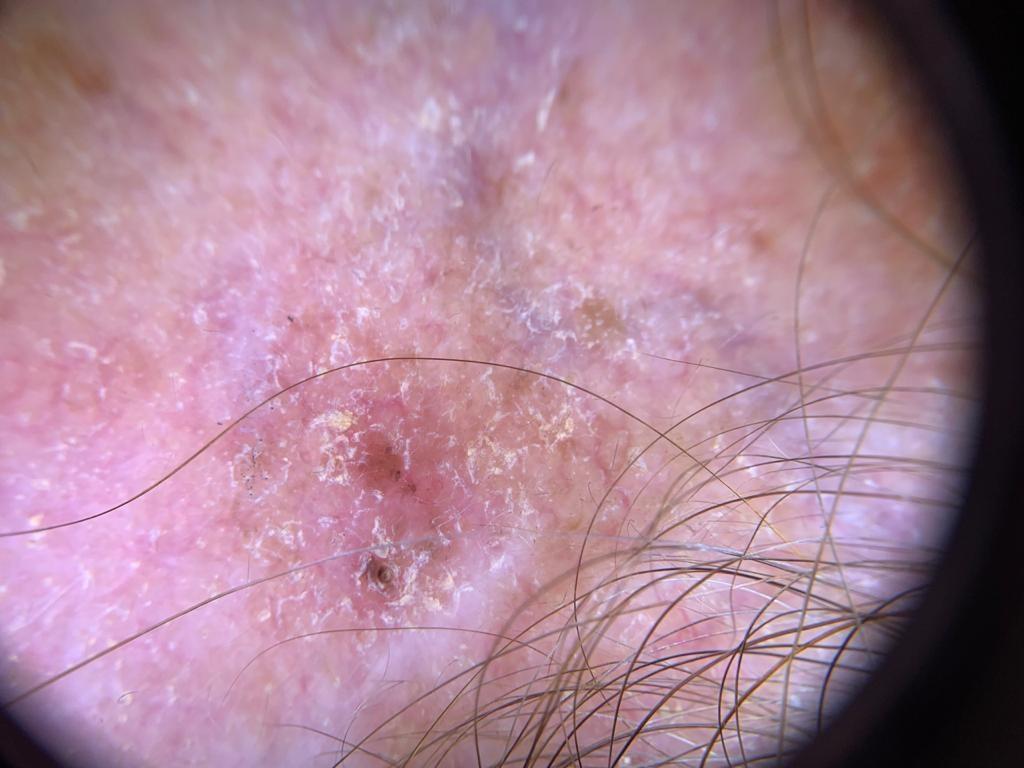  patient:
    age_approx: 65
    sex: female
  image: dermoscopy
  diagnosis:
    name: Basal cell carcinoma
    malignancy: malignant
    confirmation: histopathology
    lineage: adnexal